A dermatoscopic image of a skin lesion; a male subject, aged 43-47.
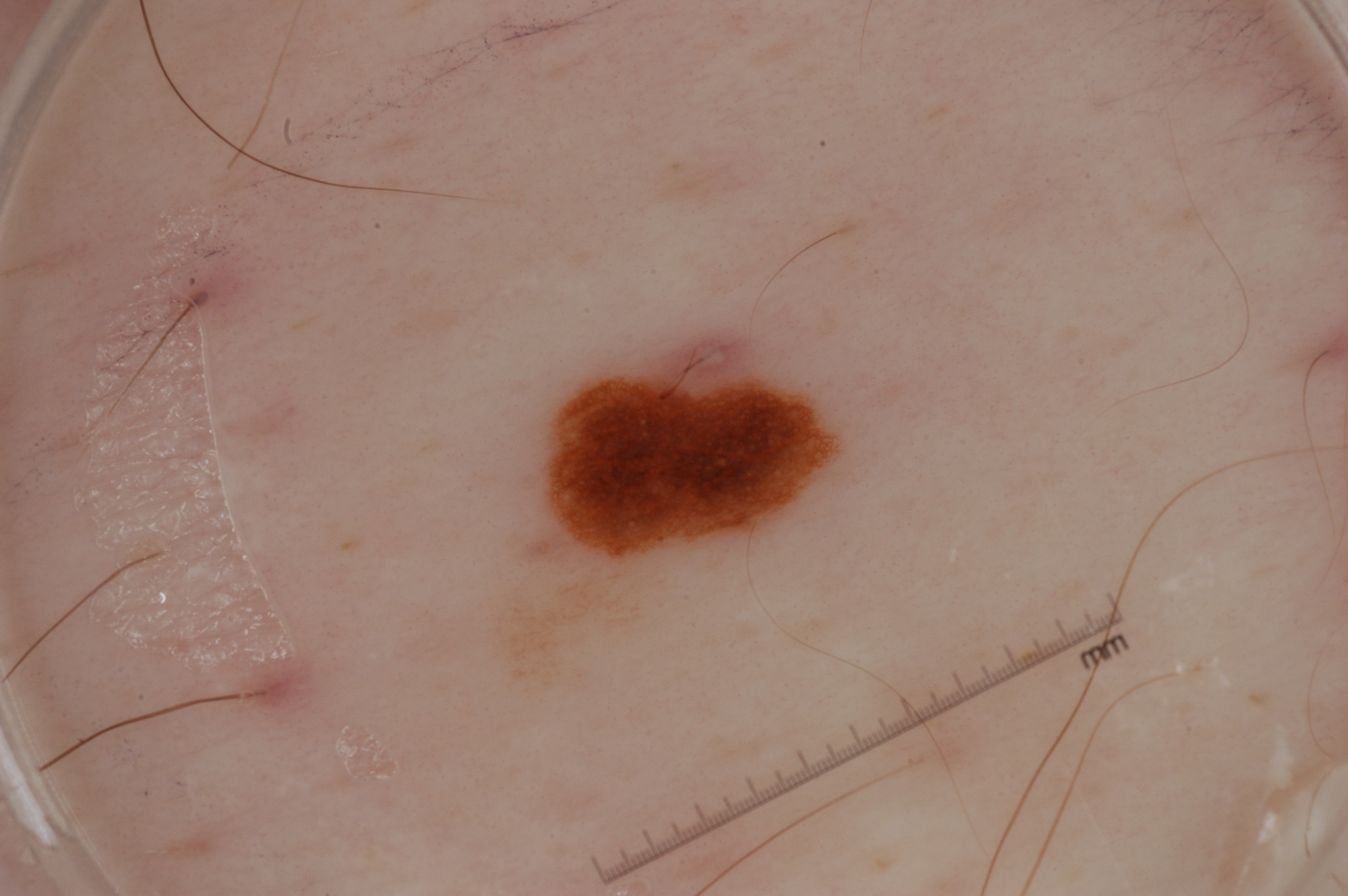A small lesion within a wider field of skin. On dermoscopy, the lesion shows pigment network, with no streaks, milia-like cysts, or negative network. As (left, top, right, bottom), lesion location: [545, 344, 838, 559]. The lesion was assessed as a melanocytic nevus.